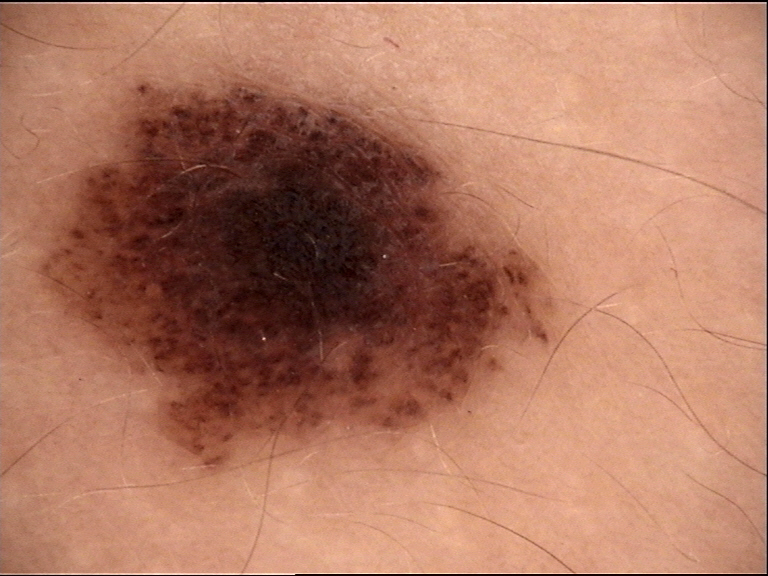A skin lesion imaged with a dermatoscope. Labeled as a dysplastic compound nevus.